A dermoscopy image of a single skin lesion.
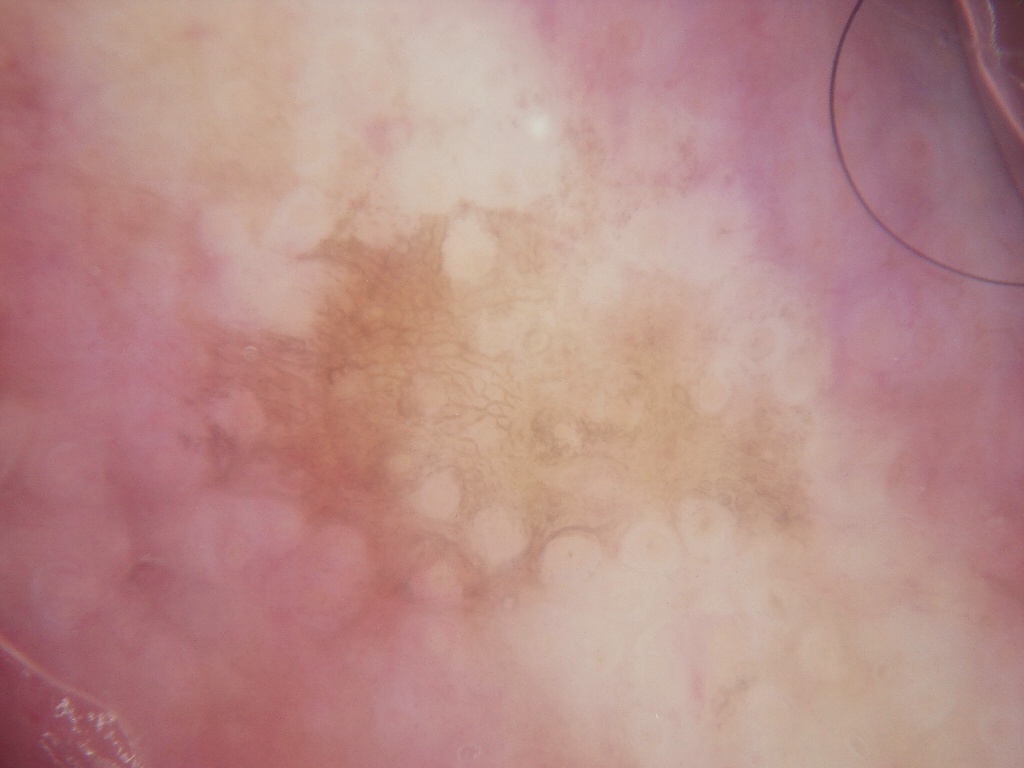Dermoscopically, the lesion shows no streaks or globules.
The lesion spans x1=156, y1=110, x2=847, y2=631.
A large lesion occupying much of the field.
Diagnosed as a benign lesion.